A dermatoscopic image of a skin lesion:
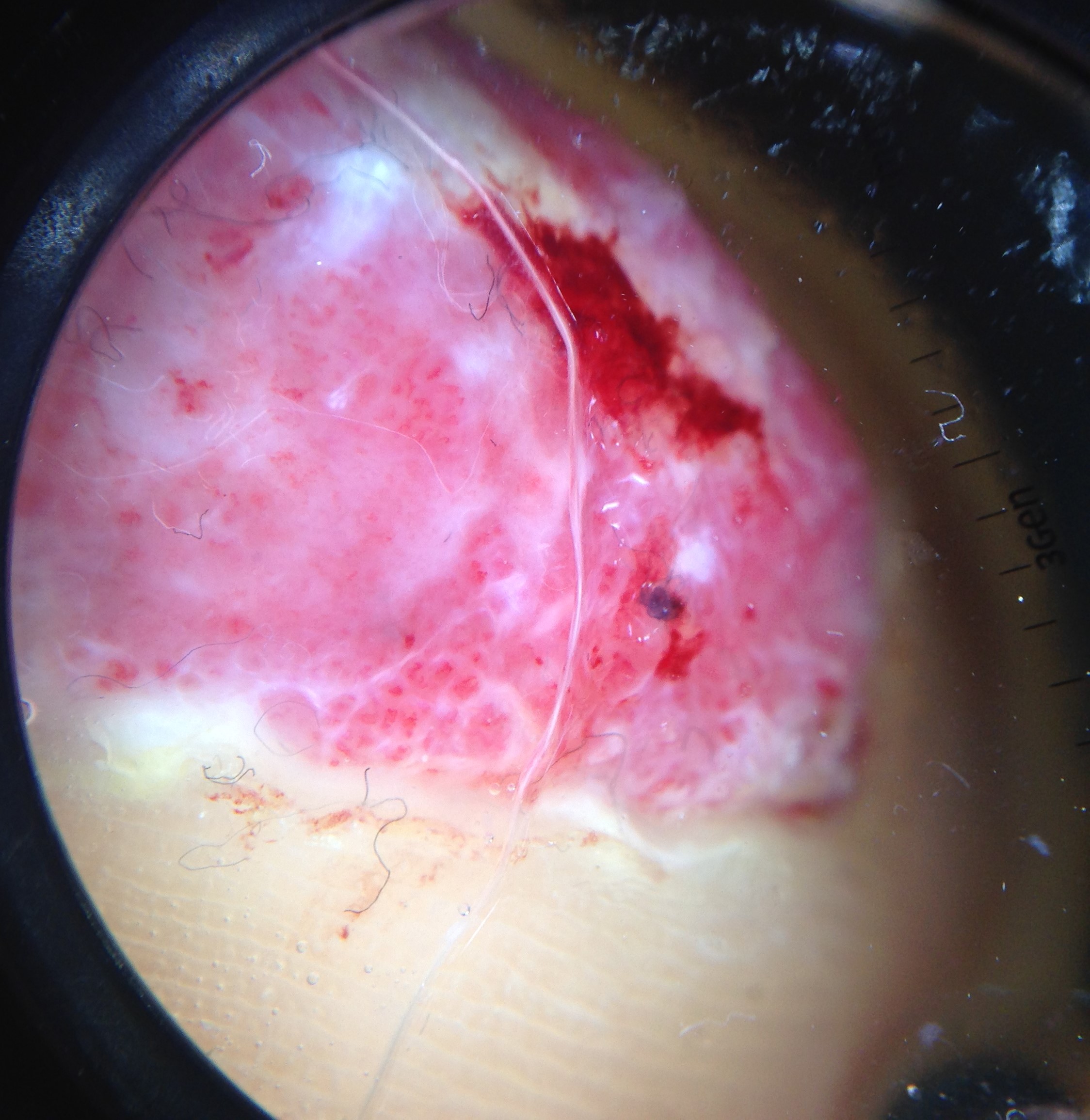Conclusion:
Histopathology confirmed a malignancy — an acral nodular melanoma.